FST IV; lay reviewers estimated MST 3 · reported duration is one to four weeks · the contributor is a female aged 50–59 · no relevant systemic symptoms · close-up view · the lesion is described as rough or flaky · the patient considered this a rash.
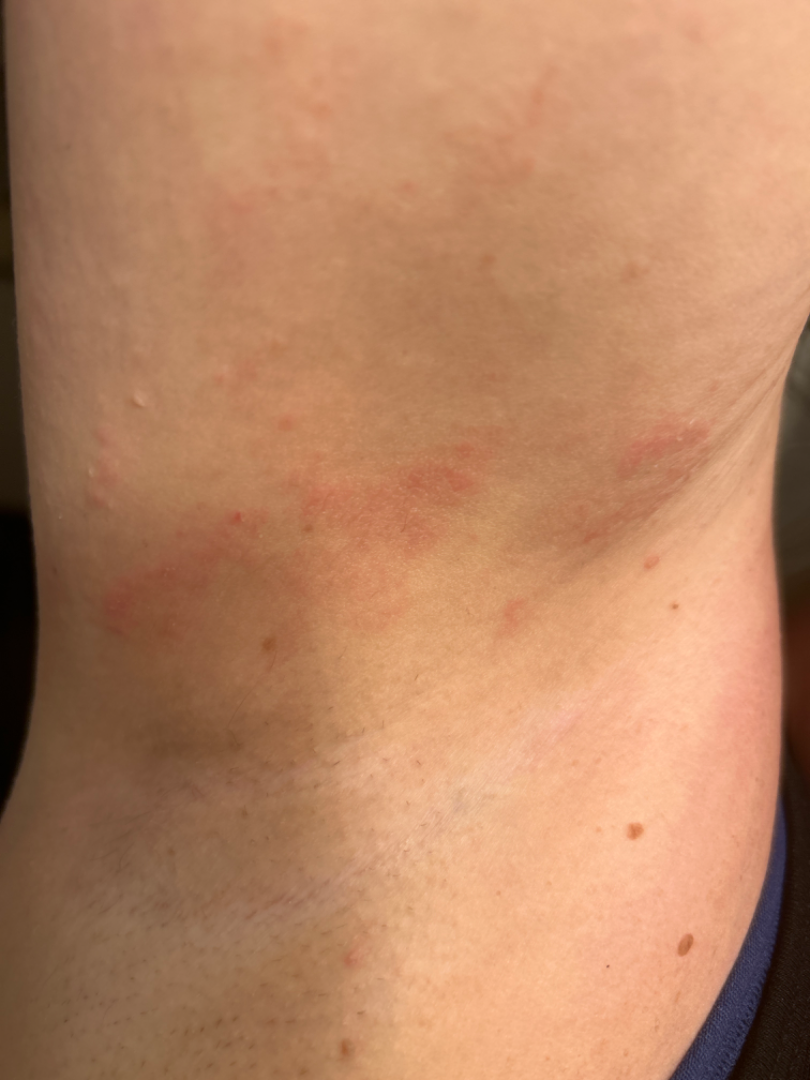assessment = could not be assessed.